The patient says their skin reddens painfully with sun exposure · the patient reports no immunosuppression · the referring clinician suspected basal cell carcinoma · a male patient age 89: 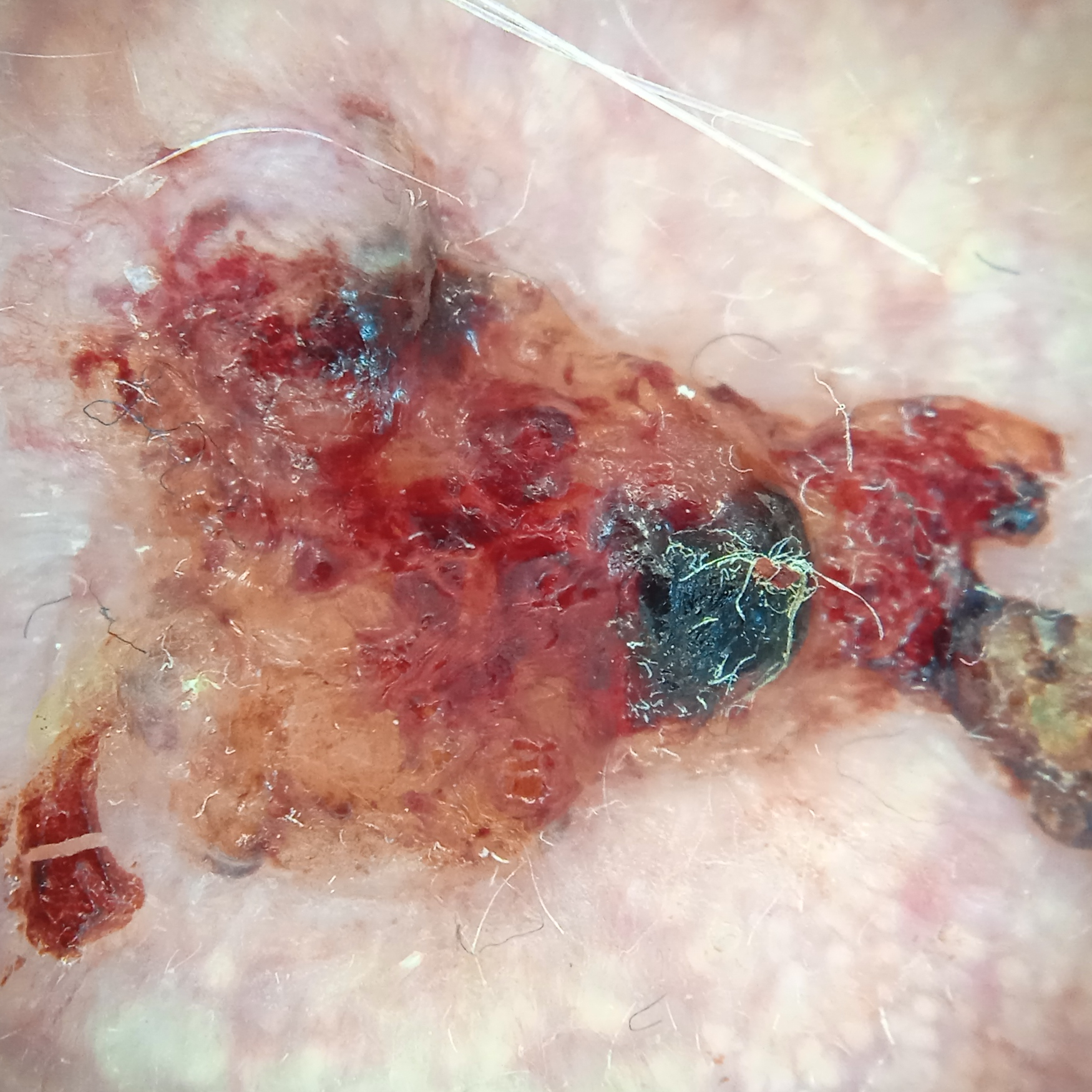Measuring roughly 14.9 mm. The biopsy diagnosis was a basal cell carcinoma, following excision, with a measured tumor thickness of 2 mm.